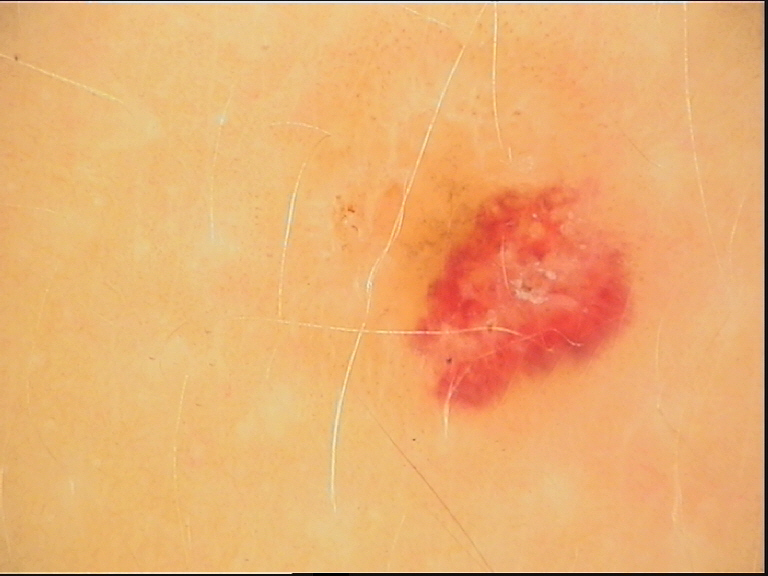The diagnosis was a hemangioma.